Self-categorized by the patient as a rash. The contributor notes associated fatigue. The photograph was taken at a distance. The lesion is associated with itching. The contributor notes the lesion is raised or bumpy. The leg and arm are involved — 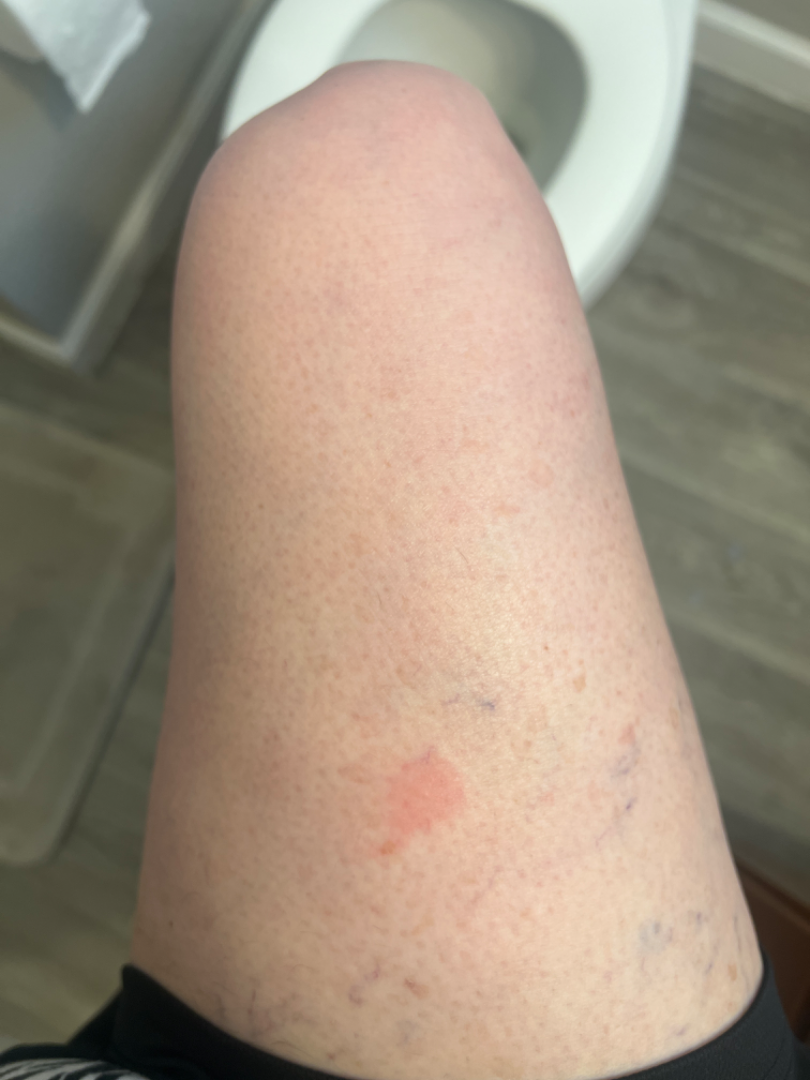differential: most consistent with Insect Bite.